A dermoscopy image of a single skin lesion.
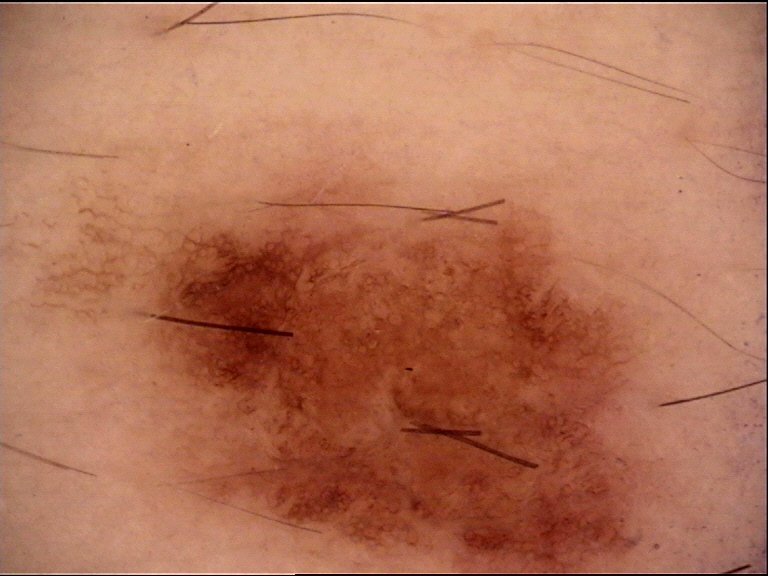diagnosis:
  name: dysplastic junctional nevus
  code: jd
  malignancy: benign
  super_class: melanocytic
  confirmation: expert consensus